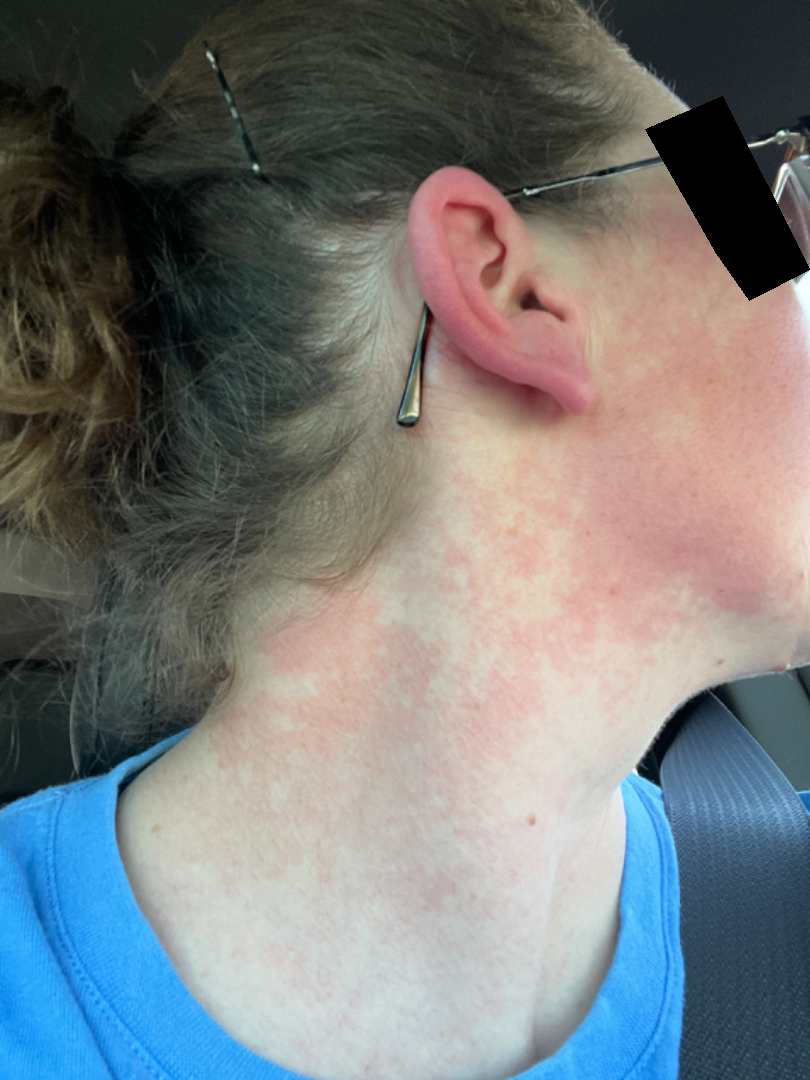location: head or neck, back of the hand, arm and leg
view: close-up
patient: female, age 30–39
diagnostic considerations: the leading impression is Allergic Contact Dermatitis; also on the differential is Rosacea; less likely is Irritant Contact Dermatitis